The leg is involved; no associated systemic symptoms reported; the lesion is associated with itching and bothersome appearance; self-categorized by the patient as a rash; texture is reported as fluid-filled and raised or bumpy; the contributor is female; an image taken at a distance:
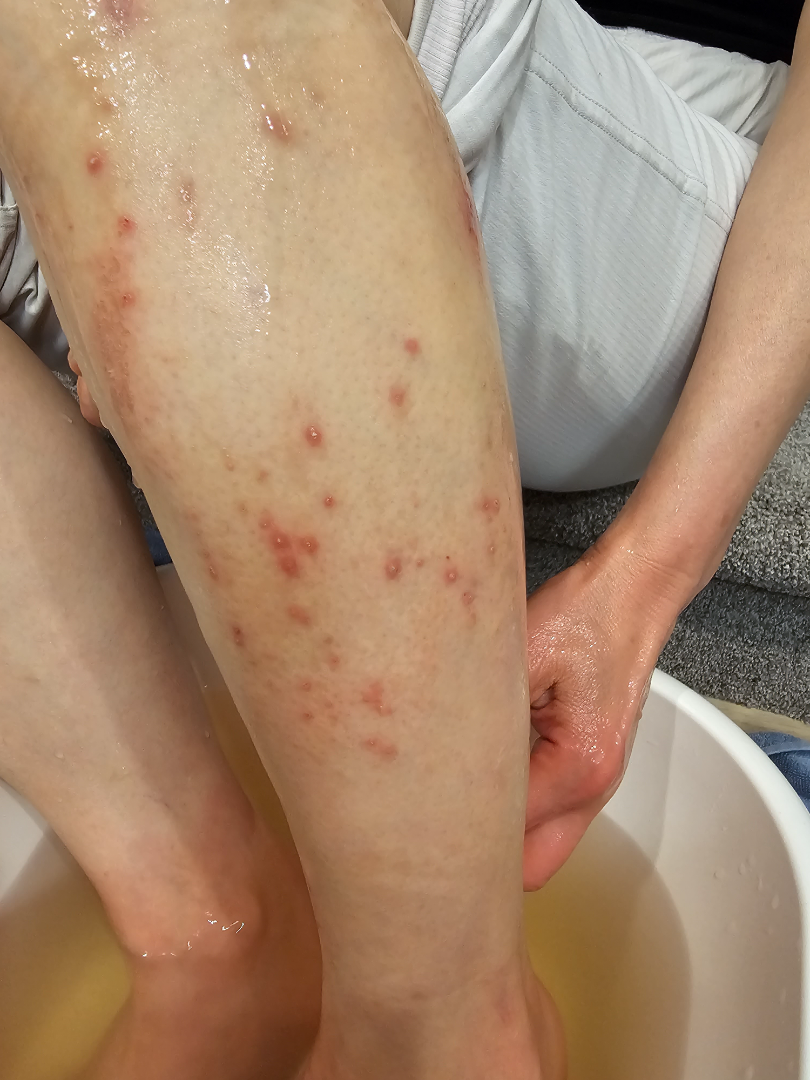impression=Perforating dermatosis and Psoriasis were each considered, in no particular order.